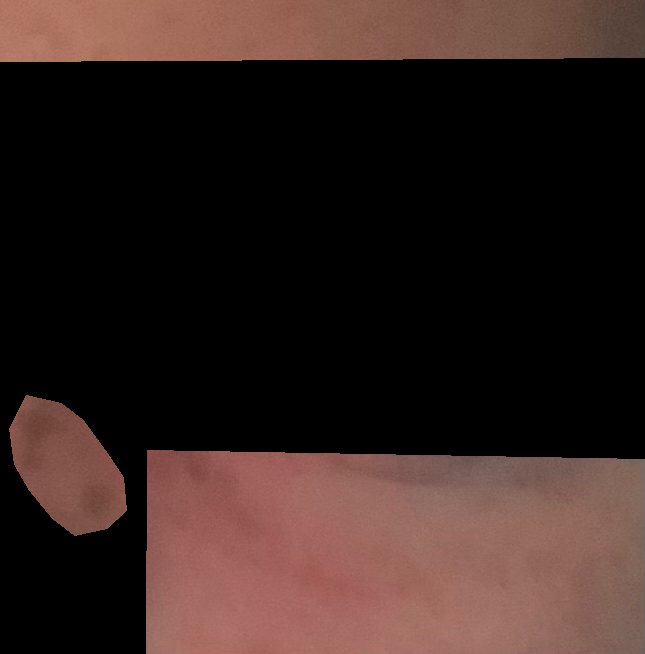The lesion is associated with itching. The patient is a female aged 18–29. The contributor notes the lesion is raised or bumpy. The photograph was taken at an angle. The affected area is the leg and head or neck. The patient reported no systemic symptoms. Present for less than one week. Fitzpatrick phototype I; lay graders estimated Monk skin tone scale 2 or 3. The patient described the issue as a rash.